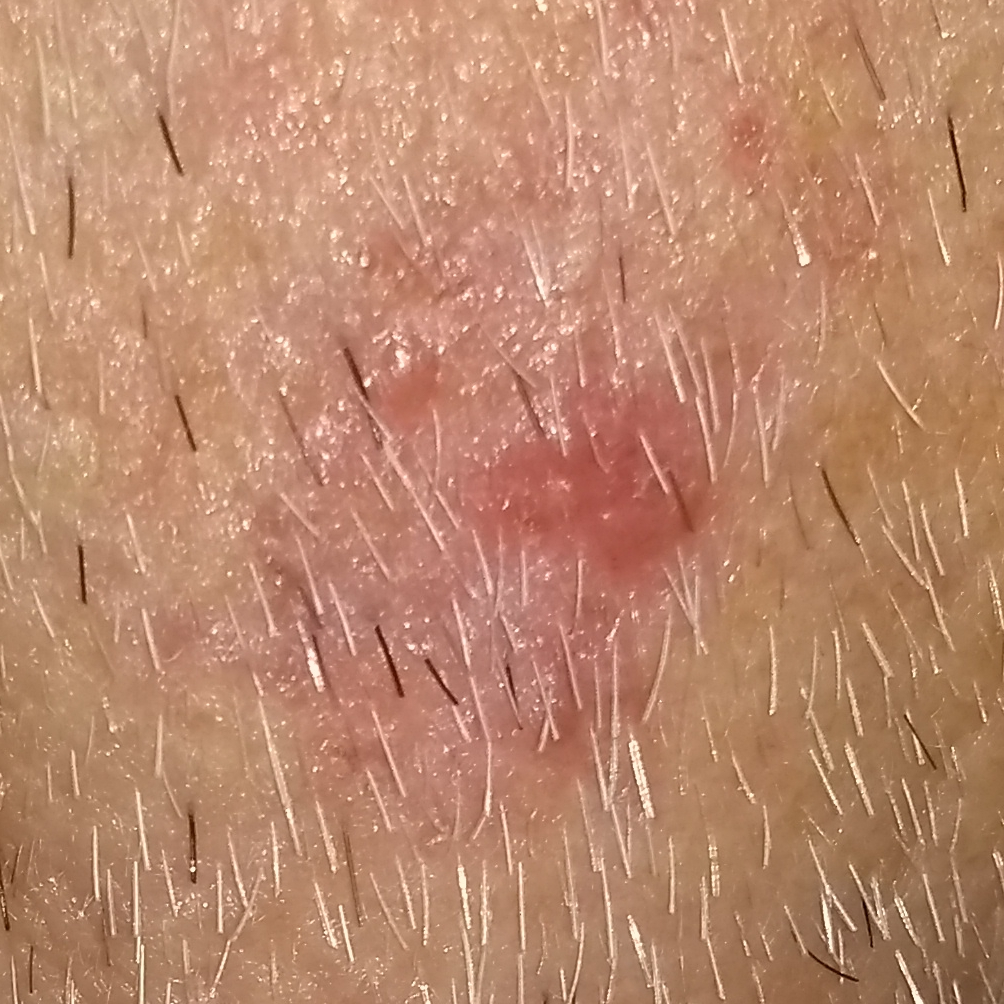Case summary:
A male patient aged 64. A clinical close-up photograph of a skin lesion. The patient was assessed as Fitzpatrick phototype III. History notes alcohol use, prior malignancy (patient or family), pesticide exposure, prior skin cancer (patient or family), and tobacco use. The lesion measures 10 × 8 mm. Per patient report, the lesion has grown, is elevated, itches, and hurts.
Pathology:
Biopsy-confirmed as a basal cell carcinoma.